A dermoscopic photograph of a skin lesion.
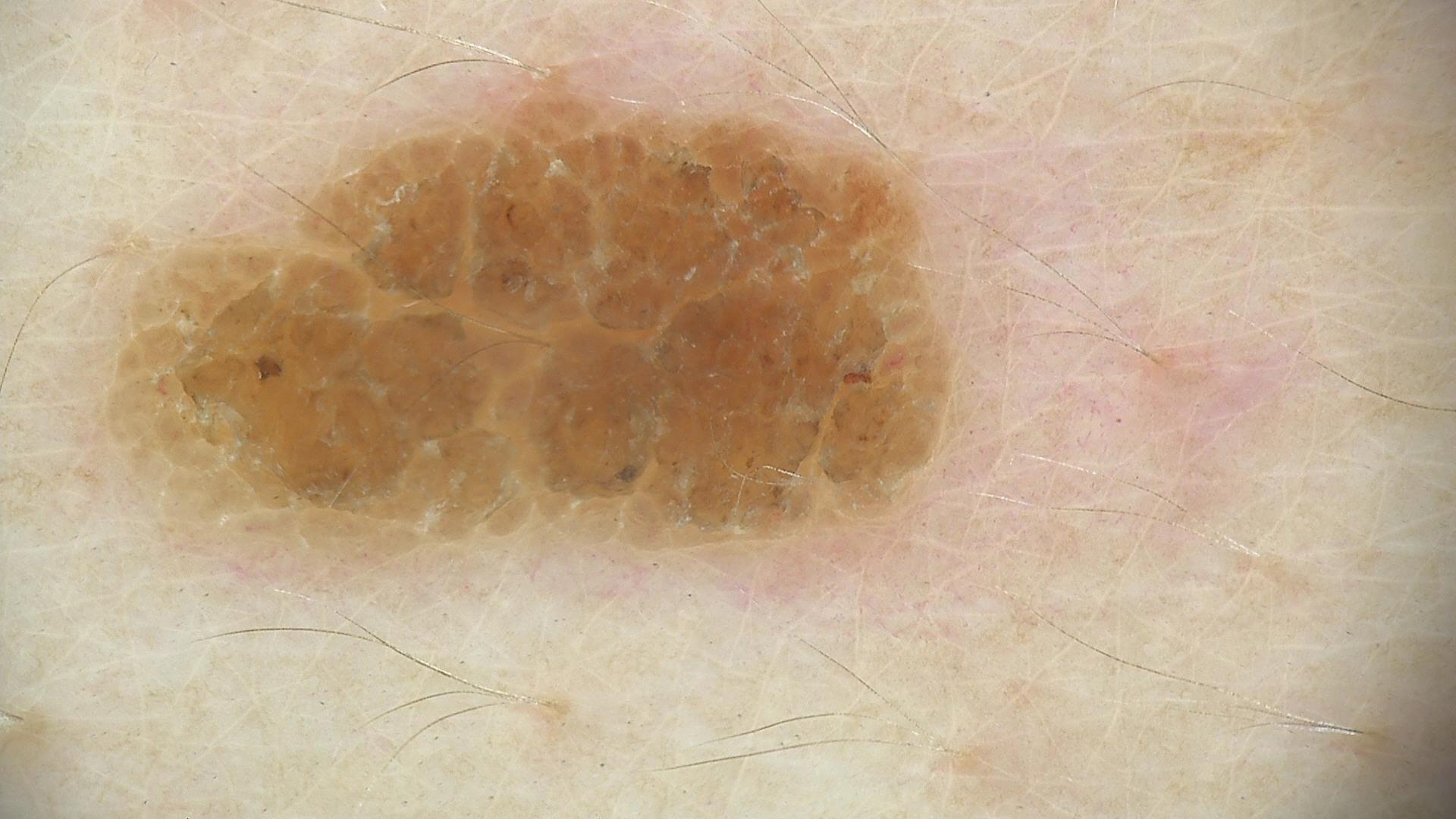lesion_type:
  main_class: keratinocytic
diagnosis:
  name: seborrheic keratosis
  code: sk
  malignancy: benign
  super_class: non-melanocytic
  confirmation: expert consensus